Female contributor, age 30–39; a close-up photograph; located on the head or neck — 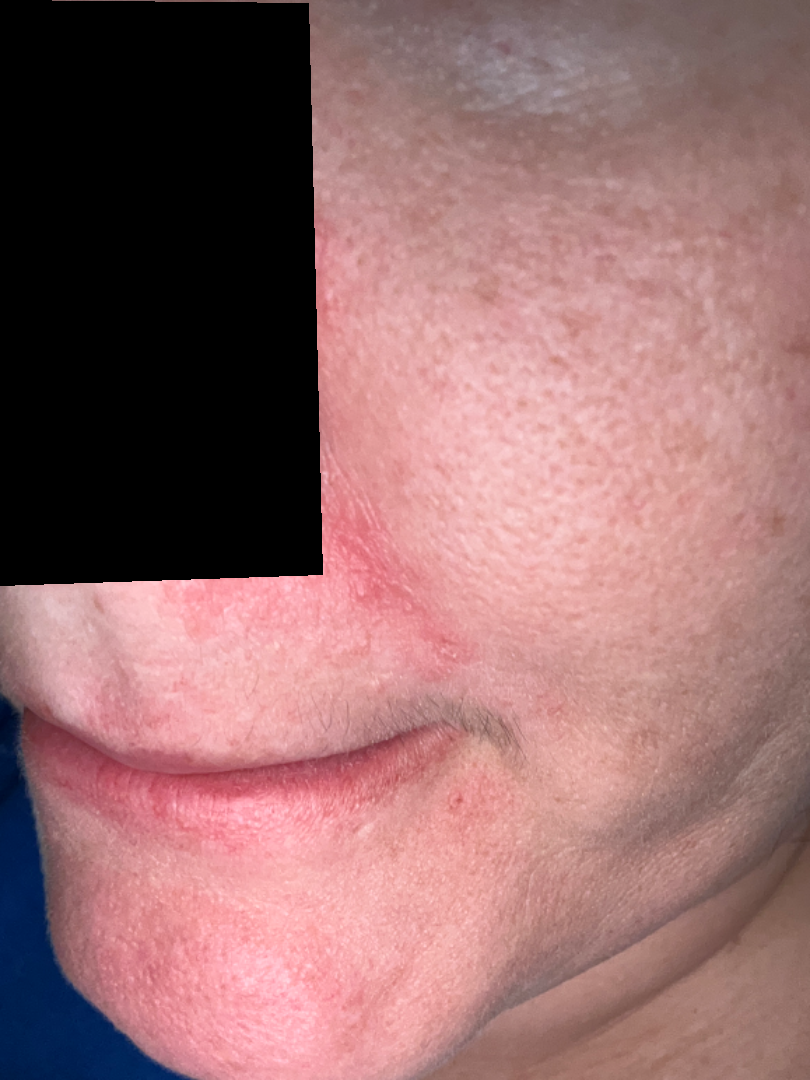{
  "differential": {
    "leading": [
      "Perioral Dermatitis"
    ]
  }
}